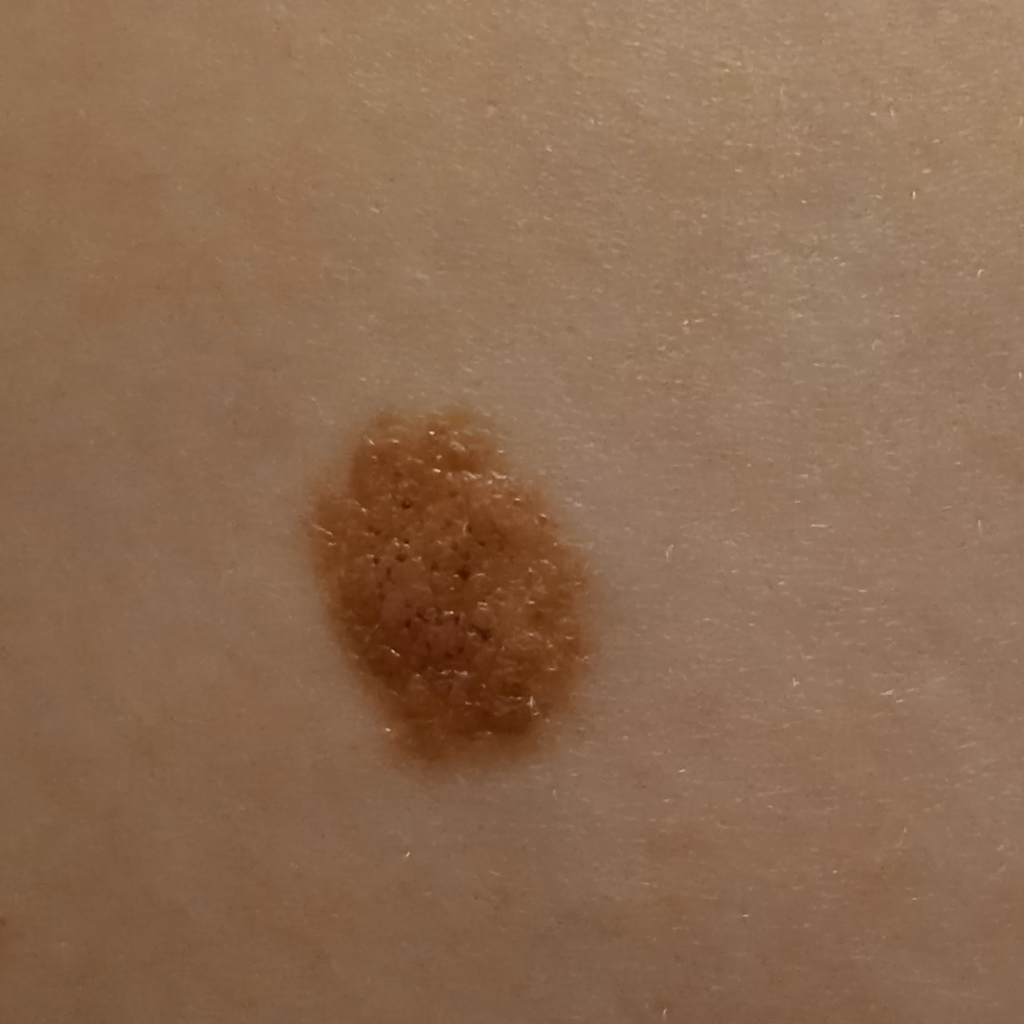• modality · clinical photo
• sun reaction · skin reddens with sun exposure
• nevus count · numerous melanocytic nevi
• referral context · research study (no referral diagnosis)
• risk factors · a history of sunbed use
• site · the torso
• diameter · 13 mm
• diagnosis · melanocytic nevus (dermatologist consensus)